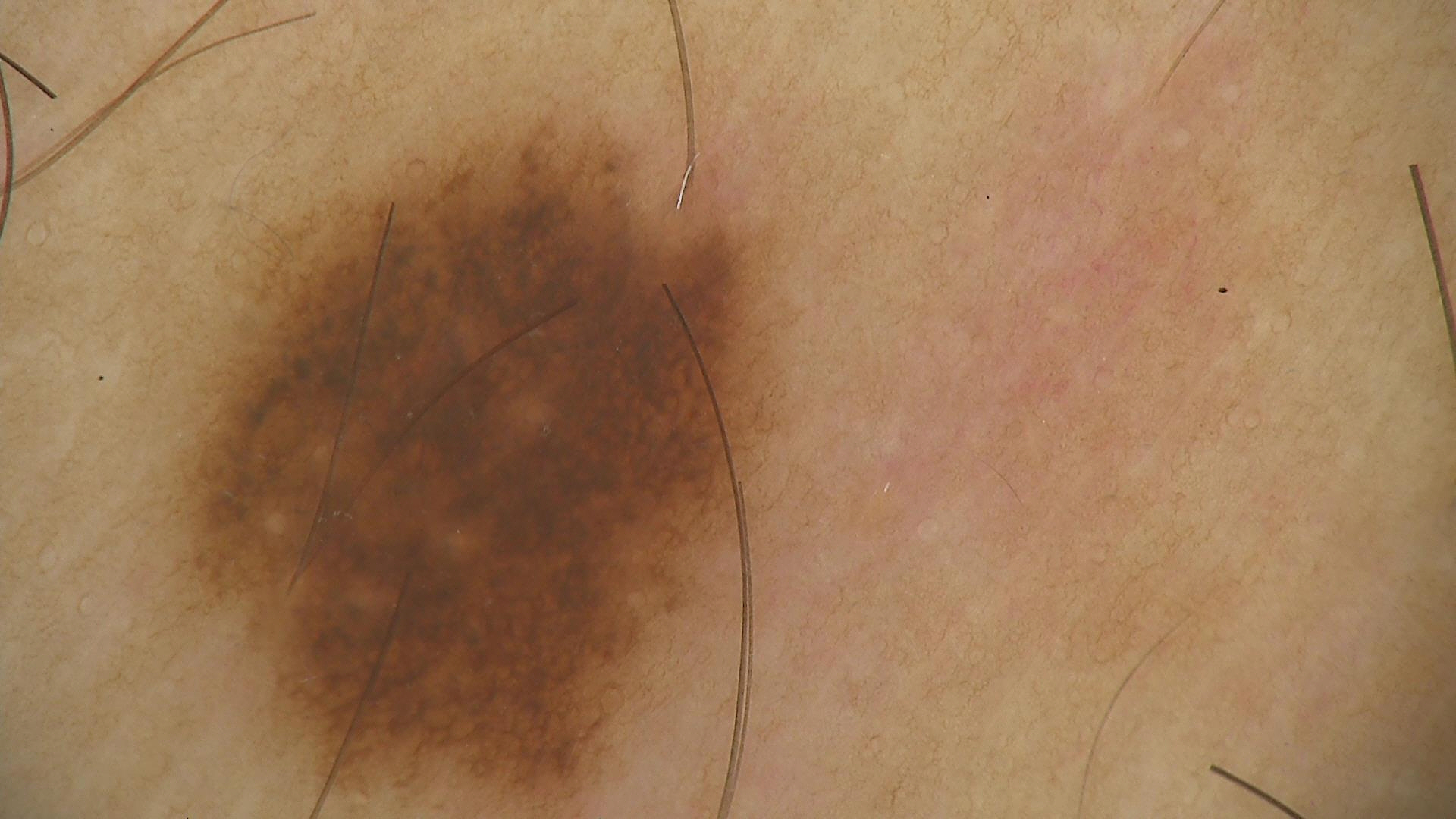The diagnostic label was a dysplastic junctional nevus.